A dermoscopic view of a skin lesion:
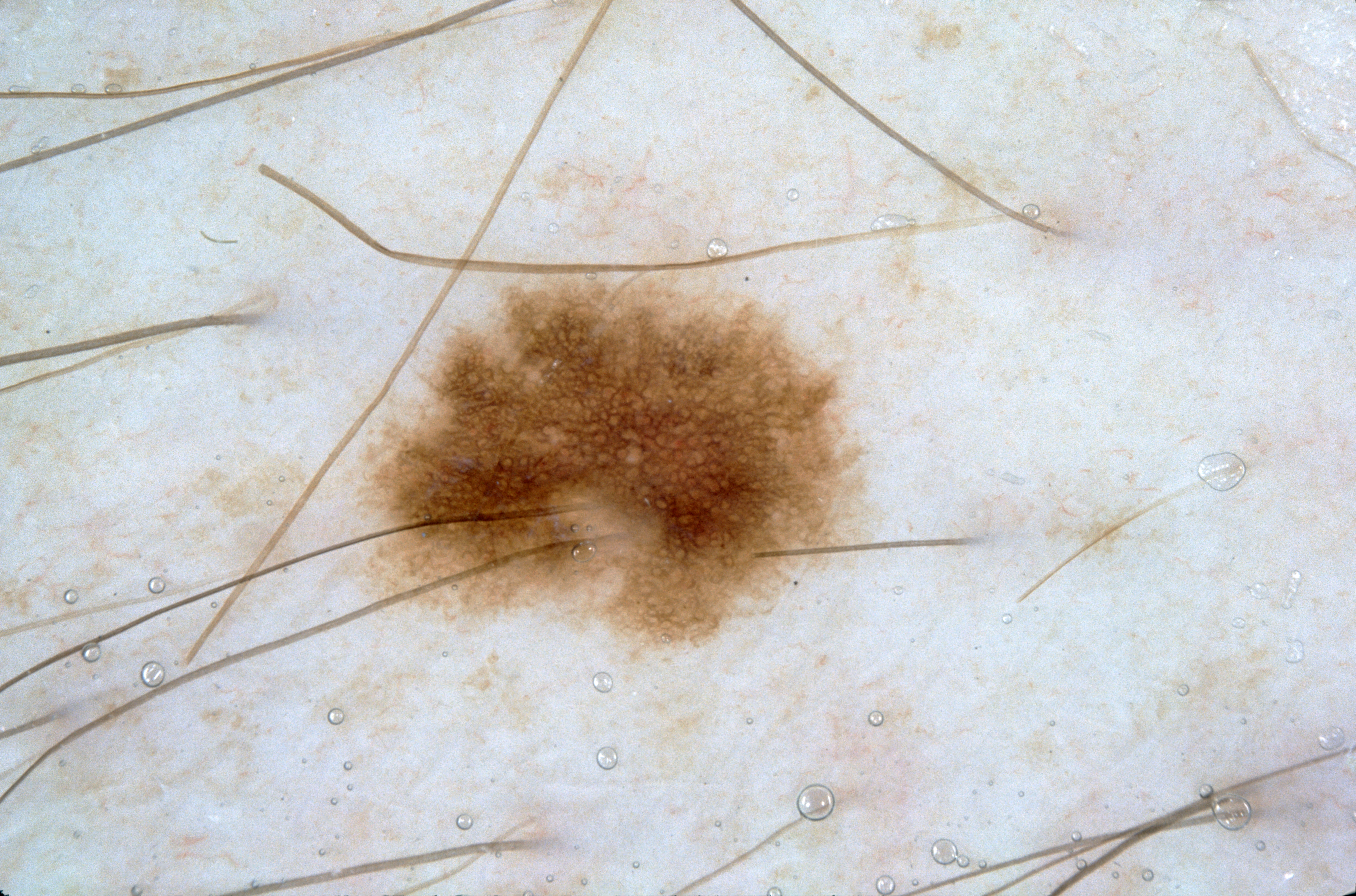lesion_location:
  bbox_xyxy:
    - 334
    - 239
    - 880
    - 683
diagnosis:
  name: melanocytic nevus
  malignancy: benign
  lineage: melanocytic
  provenance: clinical